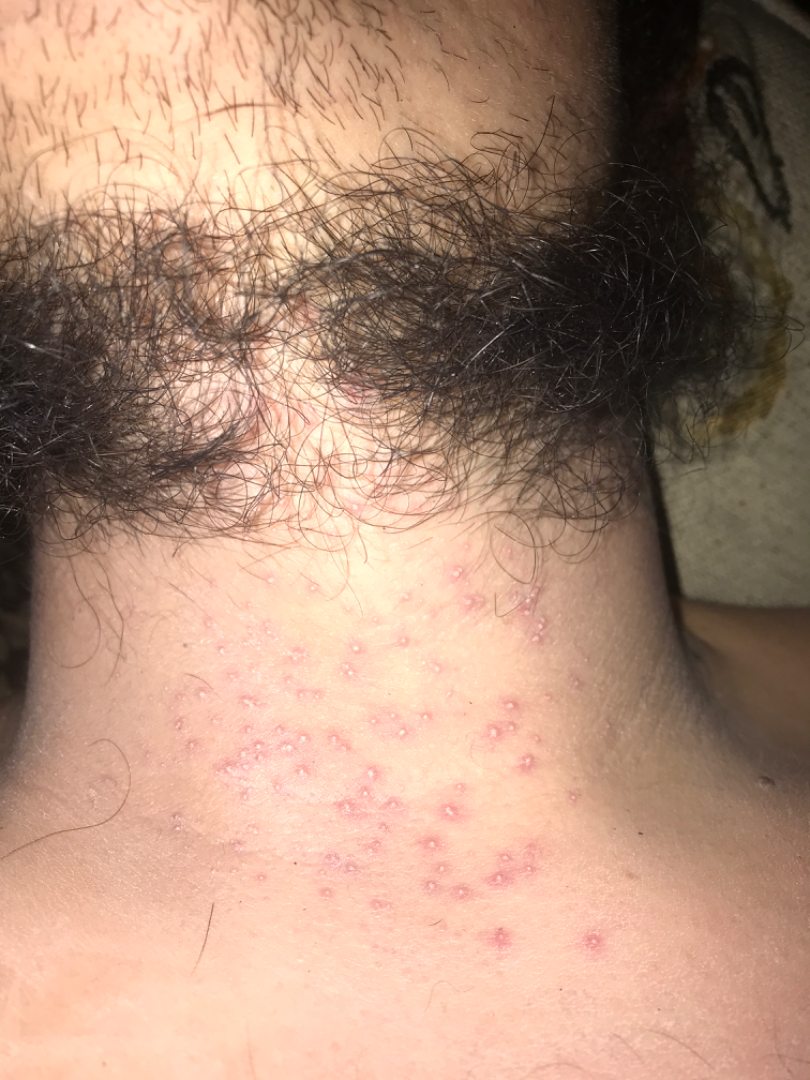Patient information:
The photograph is a close-up of the affected area. The patient indicates the lesion is raised or bumpy.
Review:
Reviewed remotely by one dermatologist: consistent with Folliculitis.